Located on the leg and arm. A close-up photograph. The patient is a male aged 40–49 — 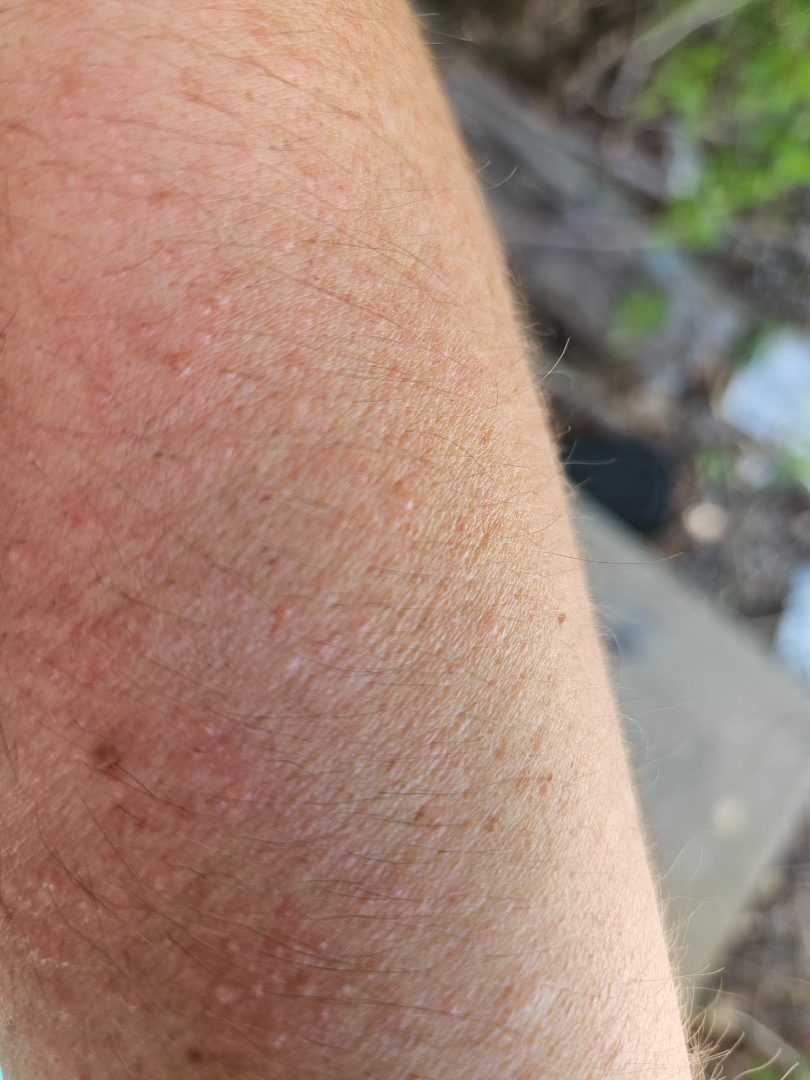The case was indeterminate on photographic review. The patient considered this a rash. Present for one to four weeks. Texture is reported as raised or bumpy. No relevant systemic symptoms. The lesion is associated with itching and bothersome appearance.